Dermoscopy of a skin lesion.
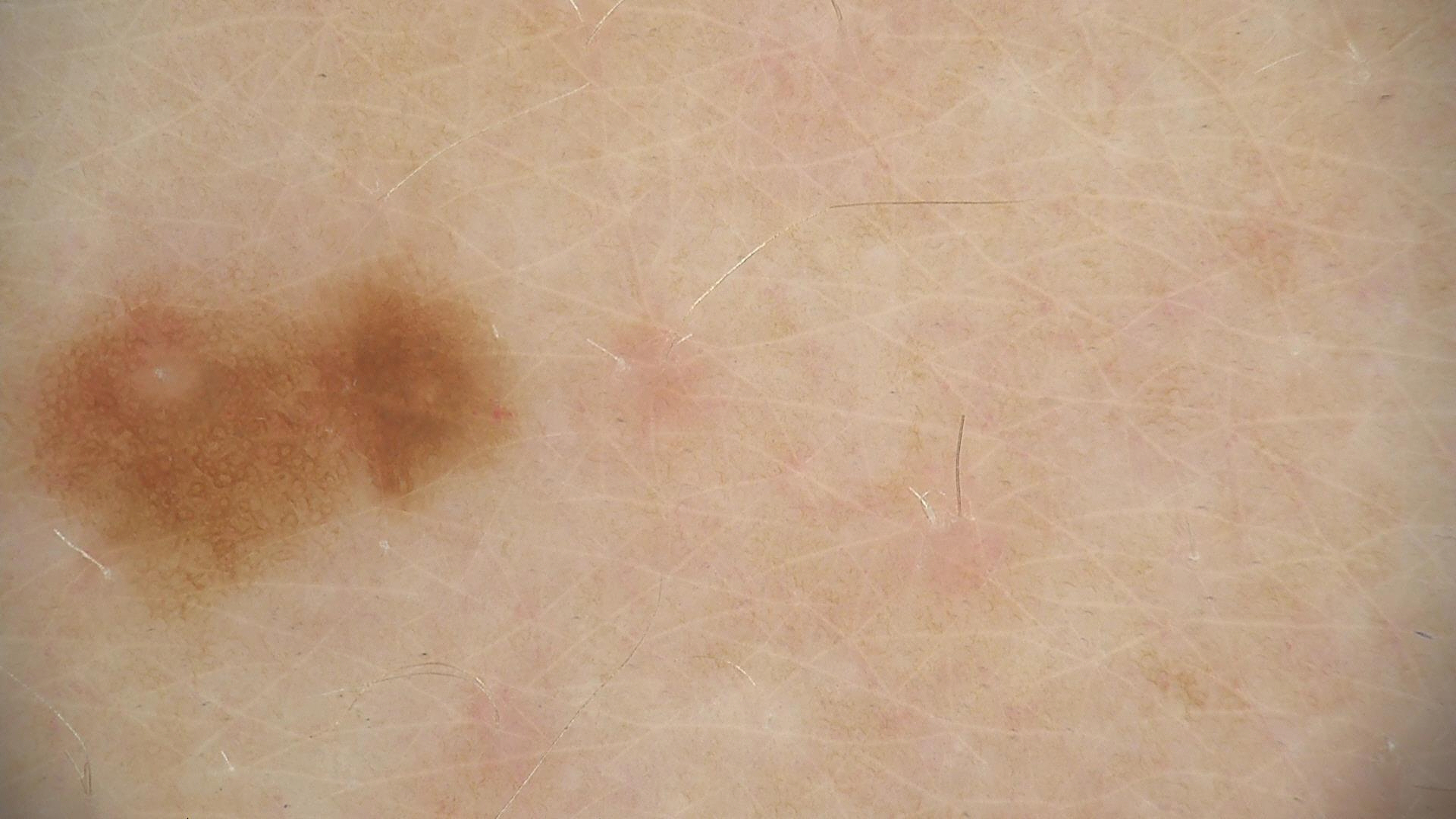The diagnosis was a dysplastic junctional nevus.